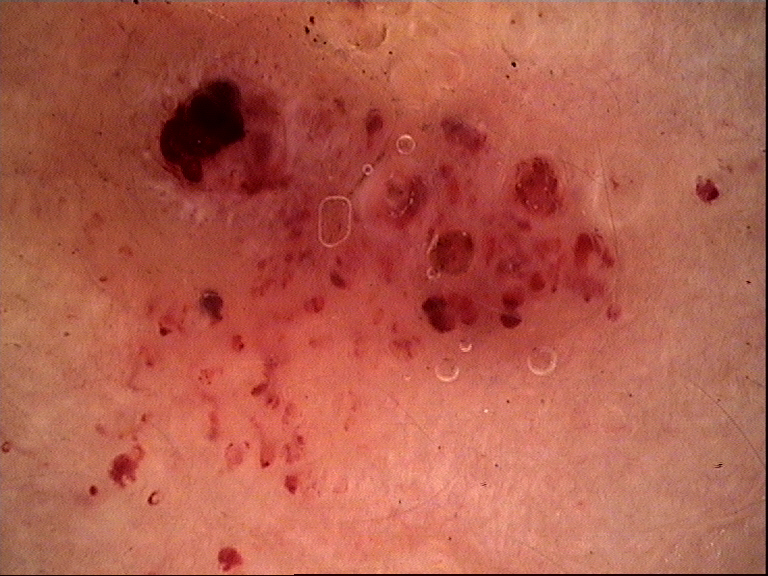Summary:
Dermoscopy of a skin lesion.
Conclusion:
Consistent with a benign lesion — a lymphangioma.